A dermoscopic image of a skin lesion.
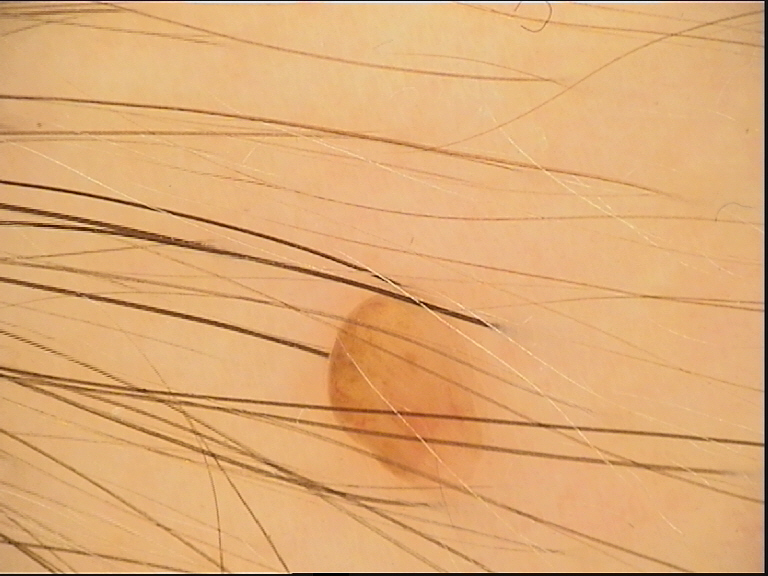{"lesion_type": {"main_class": "banal", "pattern": "dermal"}, "diagnosis": {"name": "dermal nevus", "code": "db", "malignancy": "benign", "super_class": "melanocytic", "confirmation": "expert consensus"}}